Close-up view · located on the arm and back of the torso:
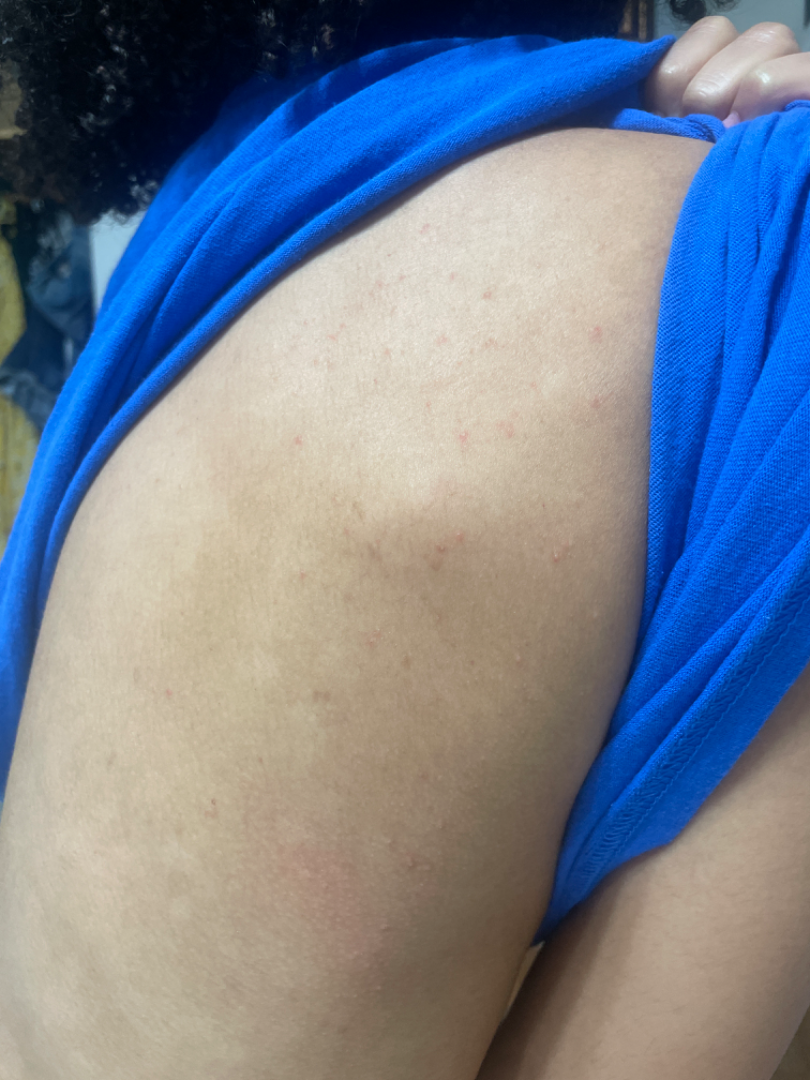  assessment: indeterminate